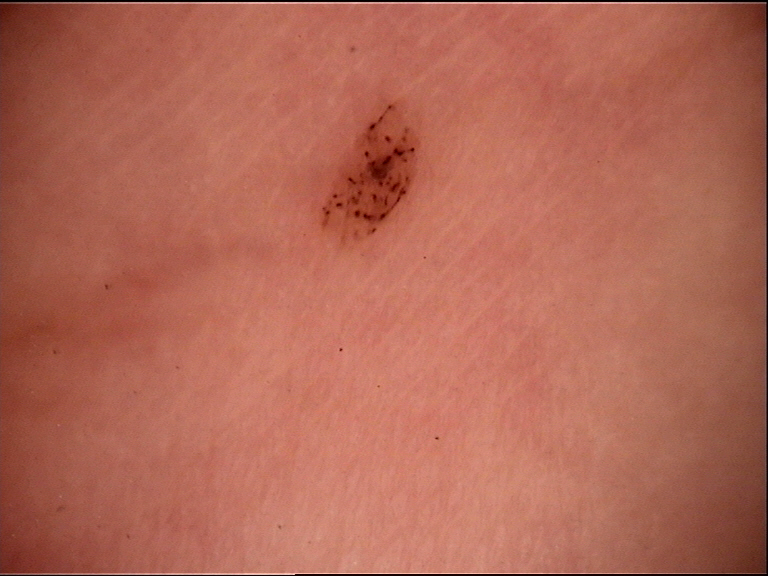Classified as an acral dysplastic junctional nevus.